This is a close-up image.
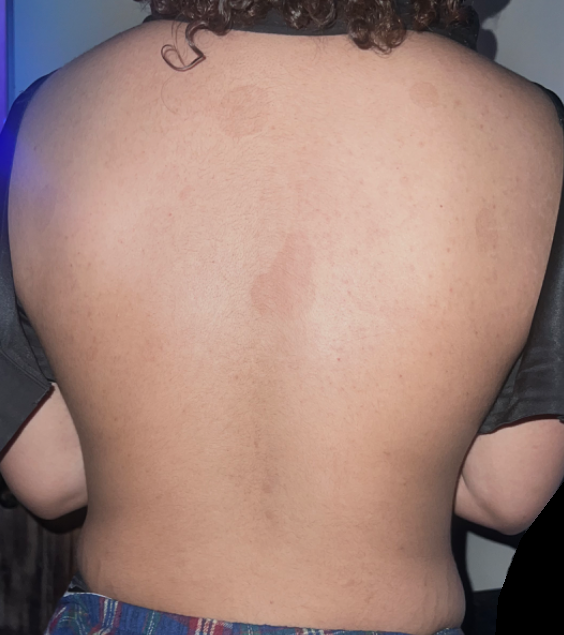No differential diagnosis could be assigned on photographic review.